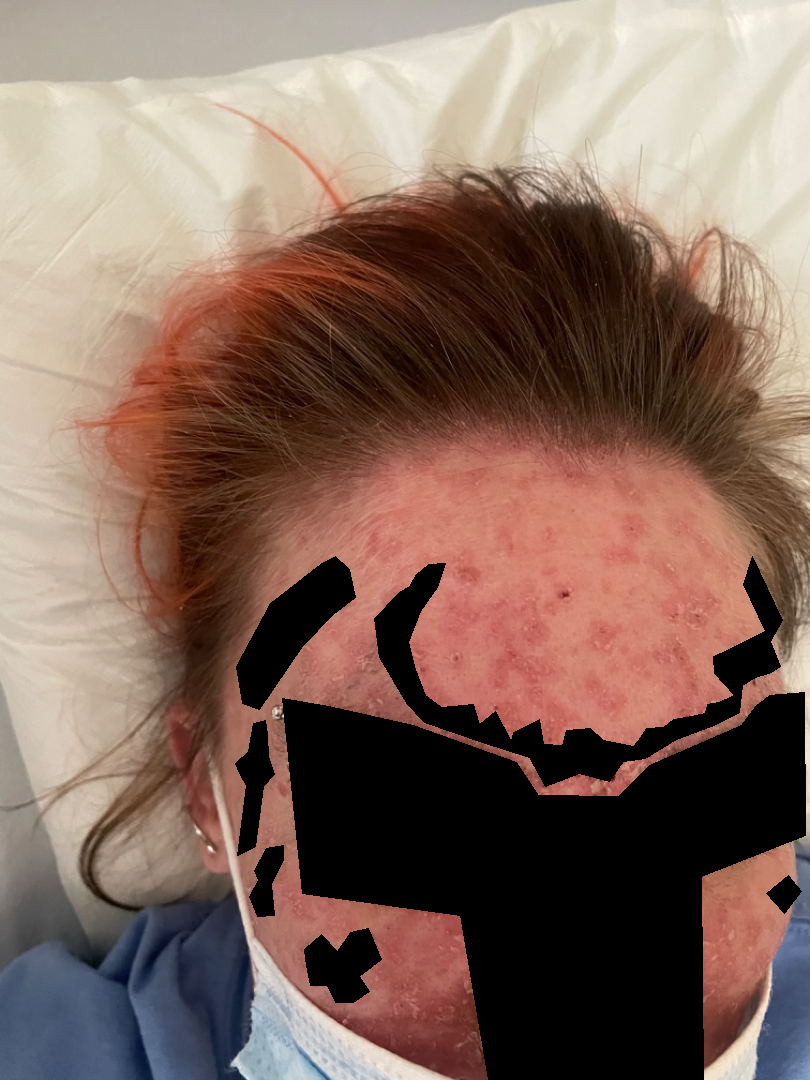assessment = ungradable on photographic review.